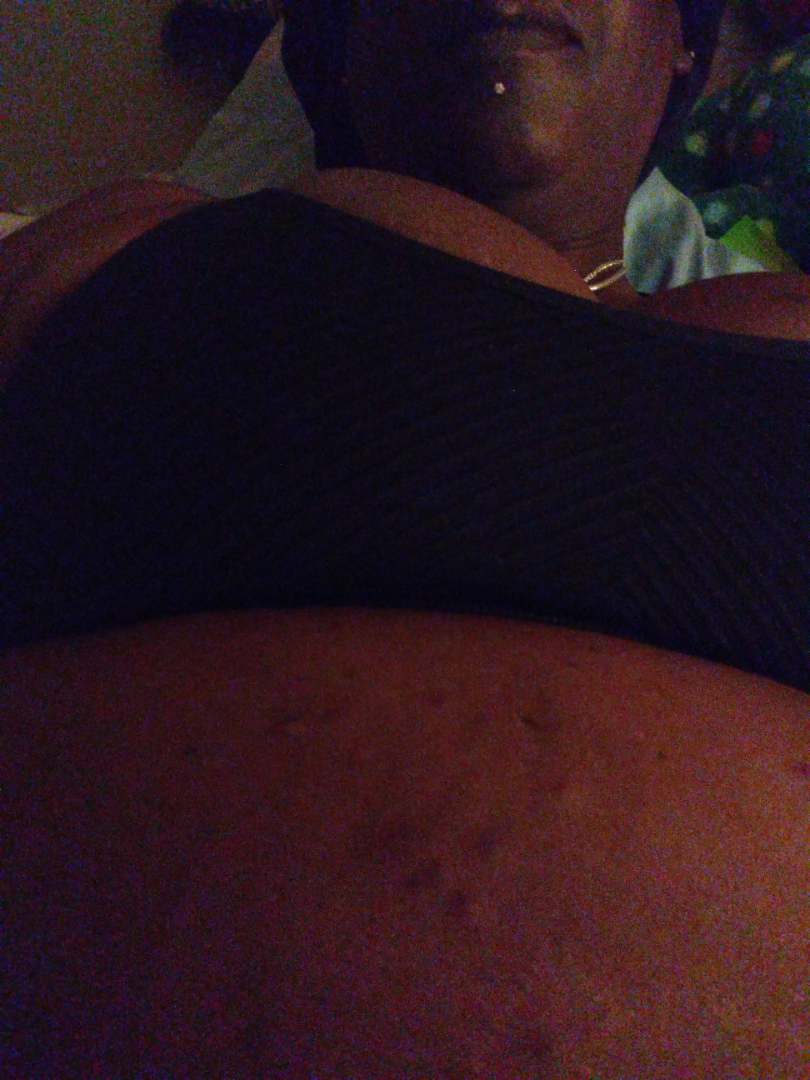The patient described the issue as skin that appeared healthy to them. The photograph was taken at an angle. The lesion is described as raised or bumpy. The subject is female. Skin tone: lay reviewers estimated MST 6. Located on the front of the torso. On dermatologist assessment of the image: the differential, in no particular order, includes Scabies and Pruritic urticarial papules and plaques of pregnancy.